A dermoscopic image of a skin lesion; the subject is a male aged 13 to 17:
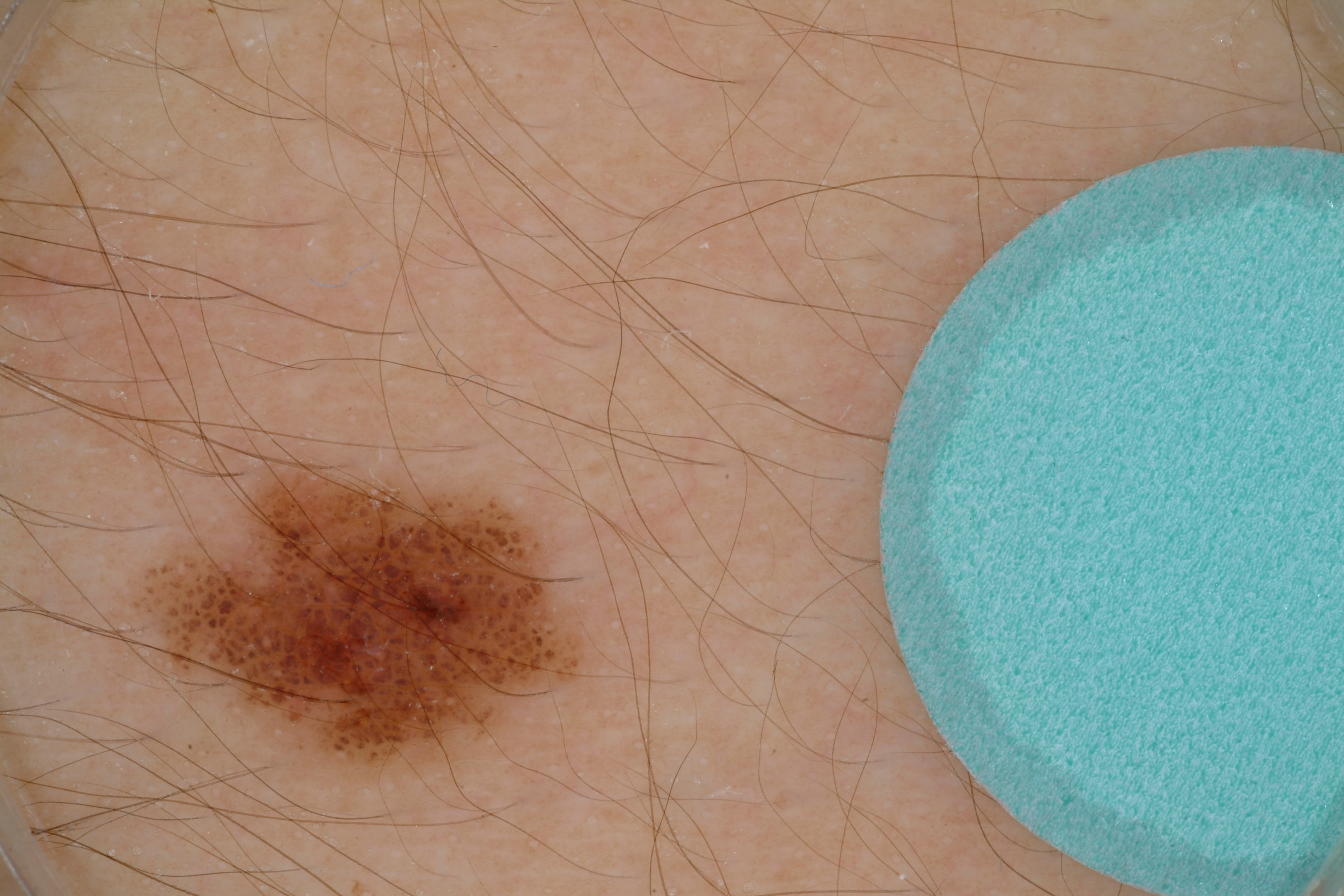Case summary: The lesion is located at left=107, top=452, right=582, bottom=776. The lesion covers approximately 9% of the dermoscopic field. Dermoscopy demonstrates no pigment network, negative network, streaks, or milia-like cysts. Conclusion: The lesion was assessed as a melanocytic nevus, a benign lesion.